A dermoscopy image of a single skin lesion.
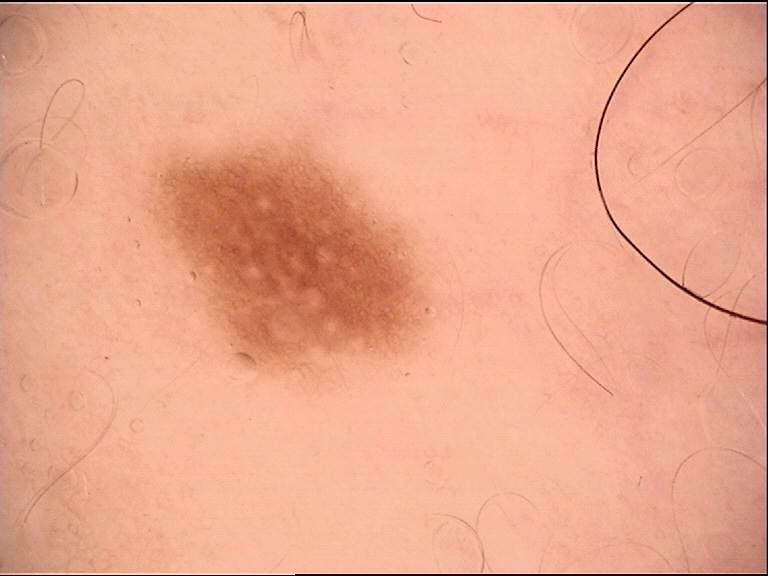Case:
• diagnosis · dysplastic junctional nevus (expert consensus)